A smartphone photograph of a skin lesion · a male patient 46 years old: 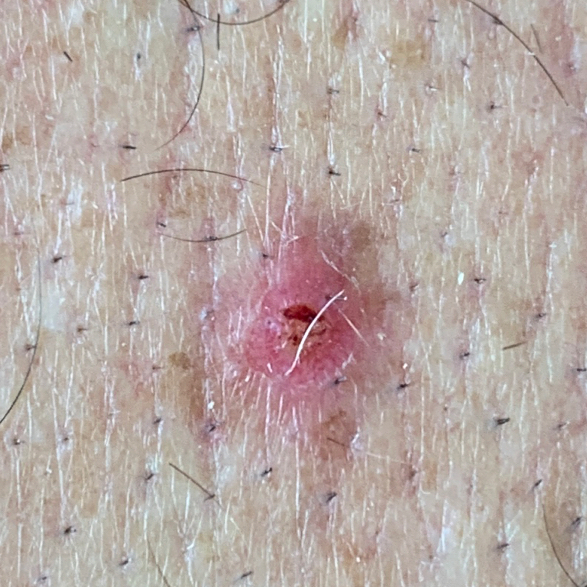location = the abdomen | pathology = actinic keratosis (biopsy-proven).